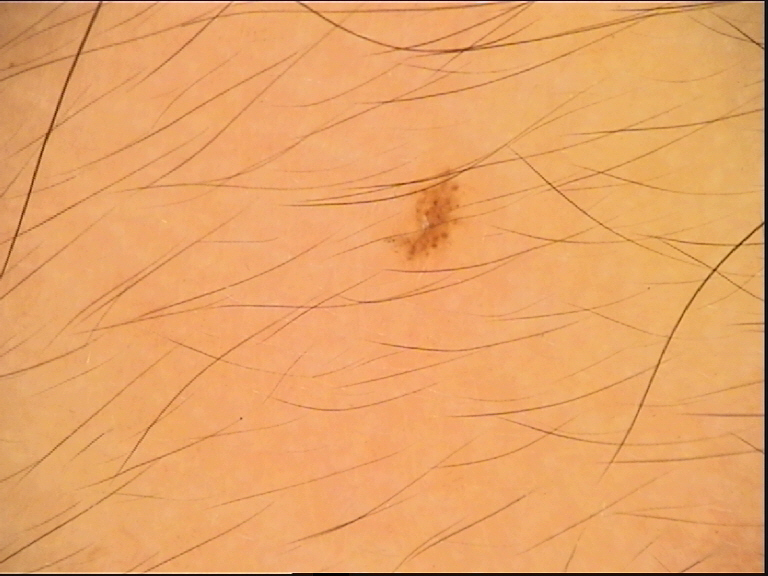Summary: A dermoscopic close-up of a skin lesion. Conclusion: Diagnosed as a benign lesion — a dysplastic junctional nevus.